The contributor is female, the condition has been present for less than one week, the patient considered this skin that appeared healthy to them, no relevant systemic symptoms, this is a close-up image, texture is reported as raised or bumpy, symptoms reported: itching and bothersome appearance, the lesion involves the front of the torso.
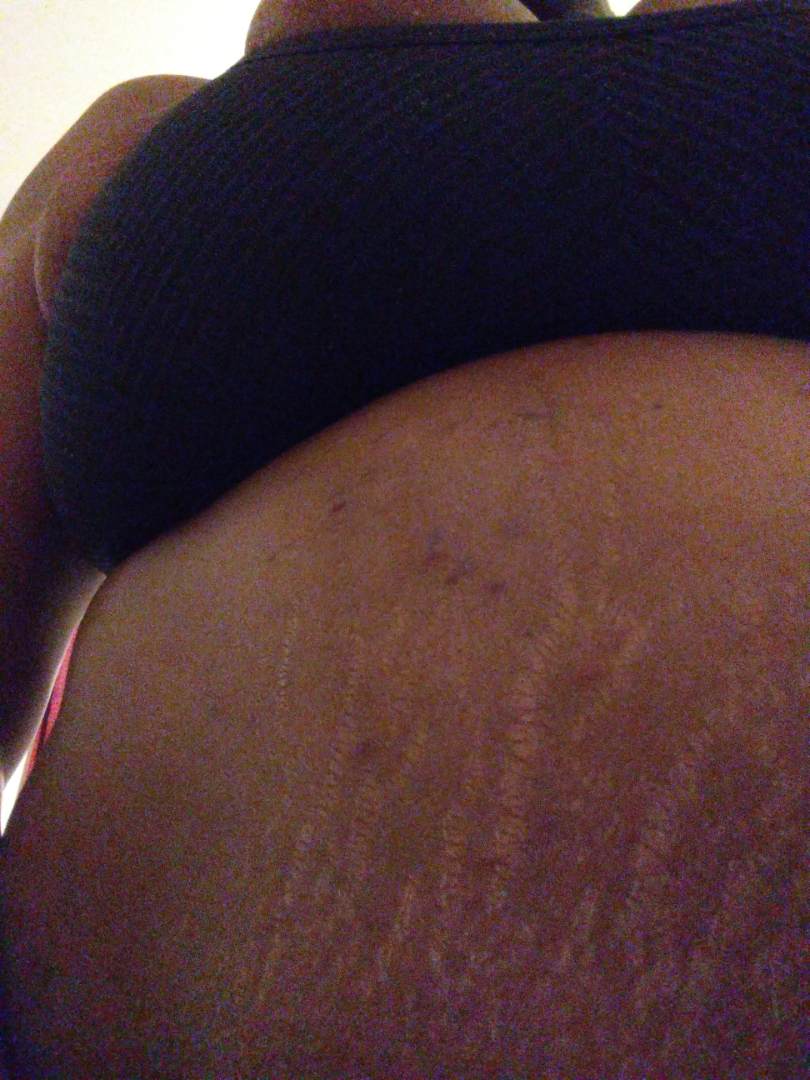Scabies and Pruritic urticarial papules and plaques of pregnancy were each considered, in no particular order.